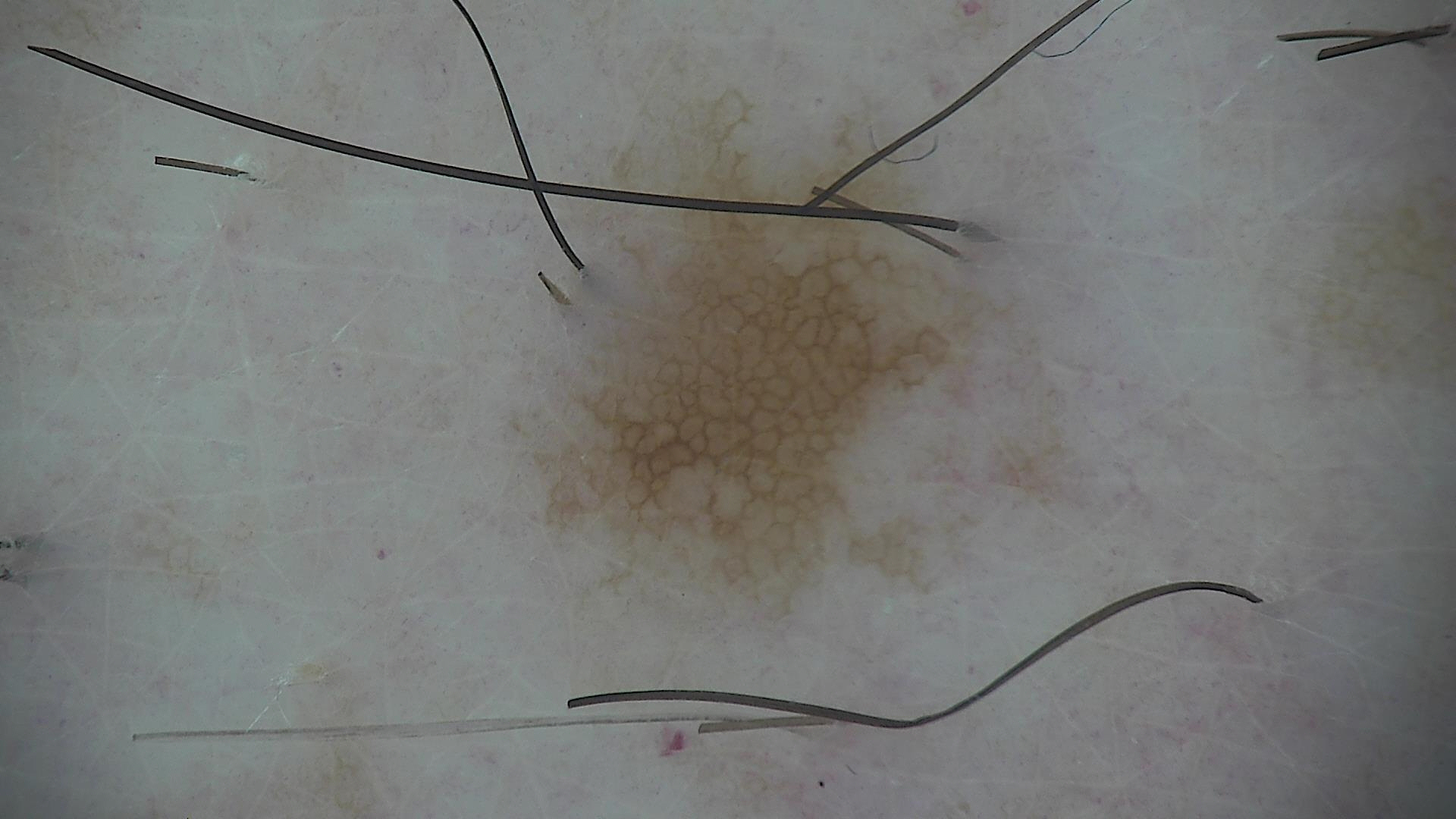imaging = dermoscopy | assessment = dysplastic junctional nevus (expert consensus).